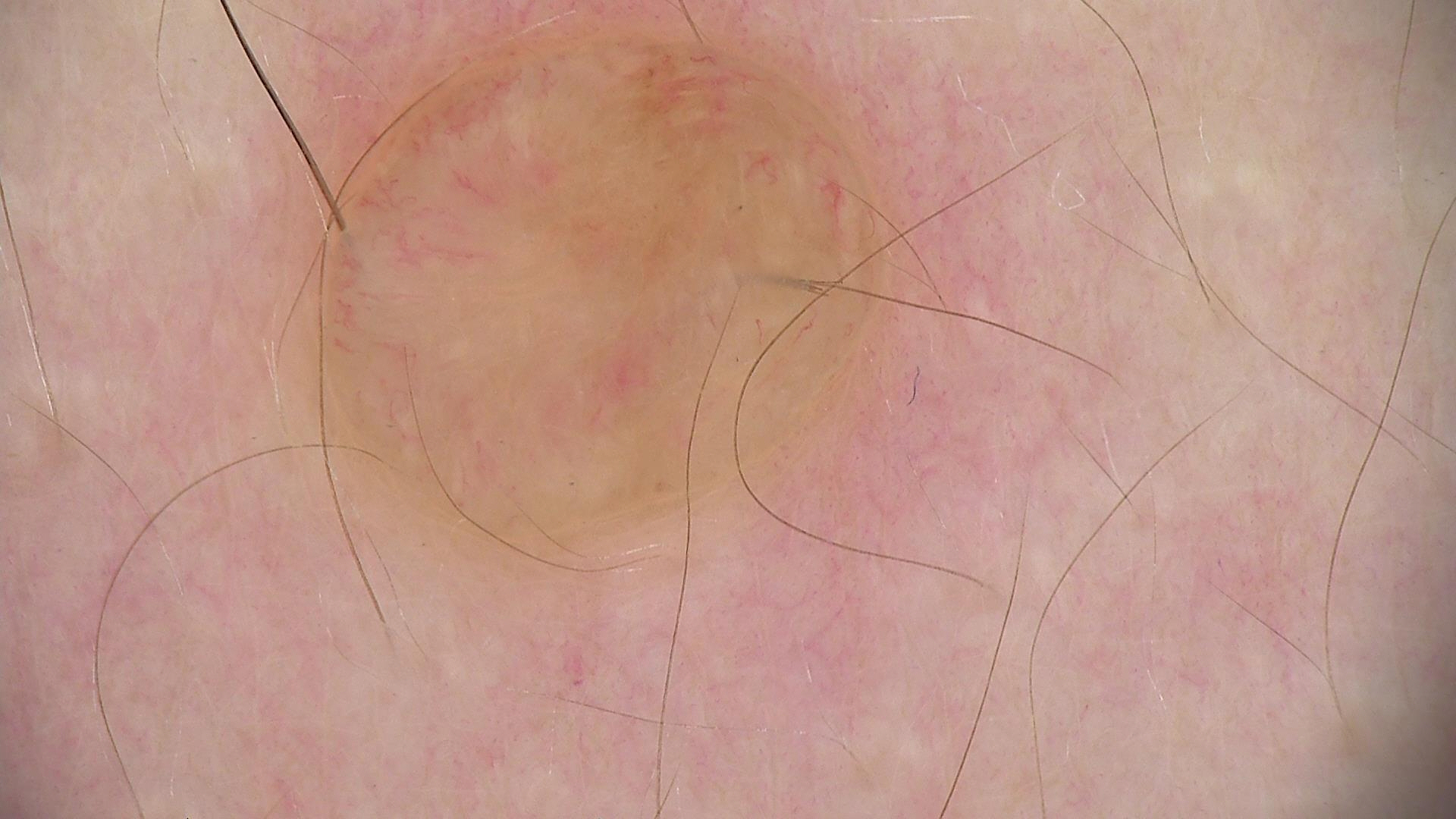Summary:
This is a banal lesion.
Conclusion:
The diagnosis was a dermal nevus.